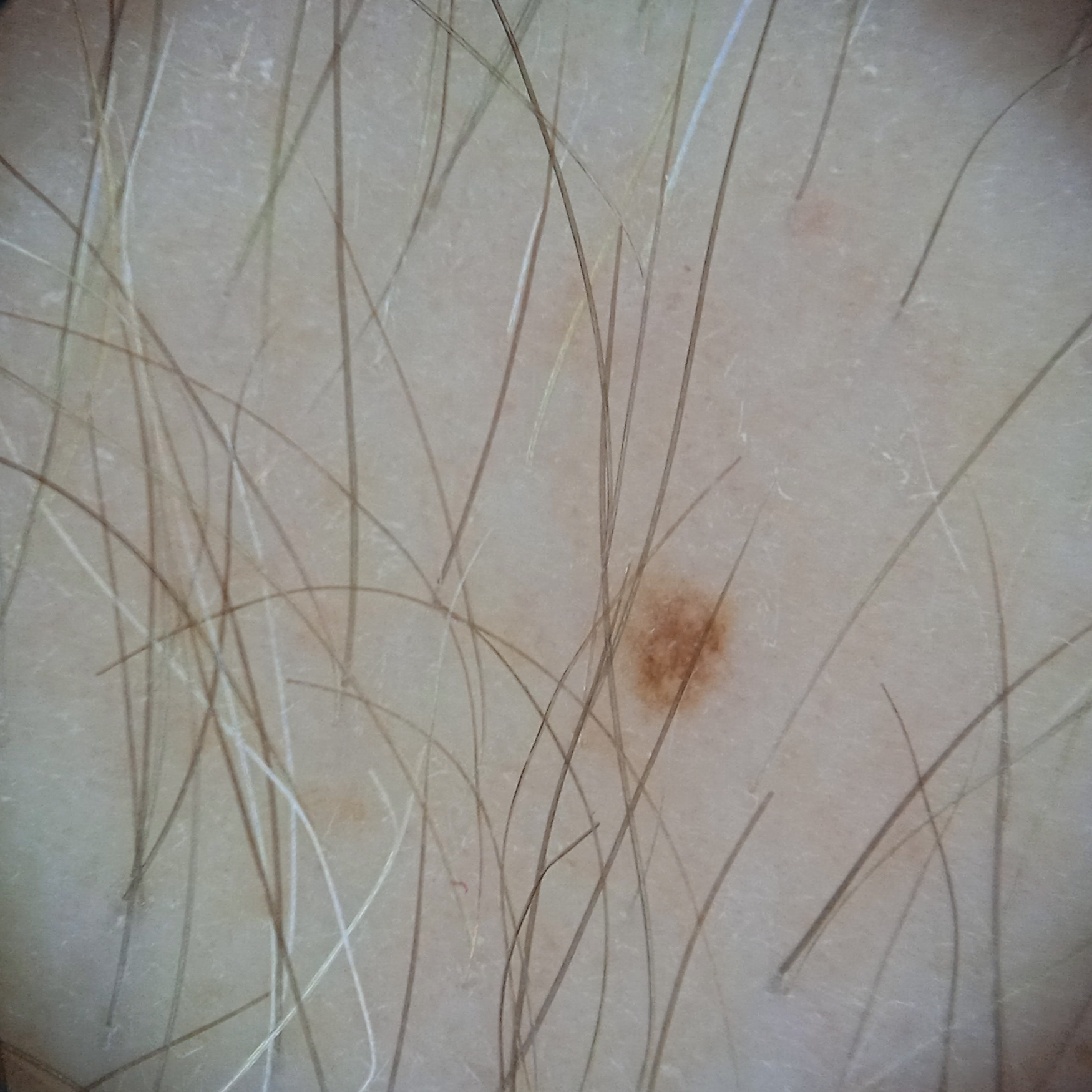The patient says their skin reddens with sun exposure. A male patient 60 years of age. Acquired for a research image collection, with no referral diagnosis. A dermoscopic image of a skin lesion. The lesion is on an arm. Measuring roughly 1.5 mm. The consensus diagnosis for this lesion was a melanocytic nevus.